Close-up view · located on the leg, arm and top or side of the foot · the subject is female: 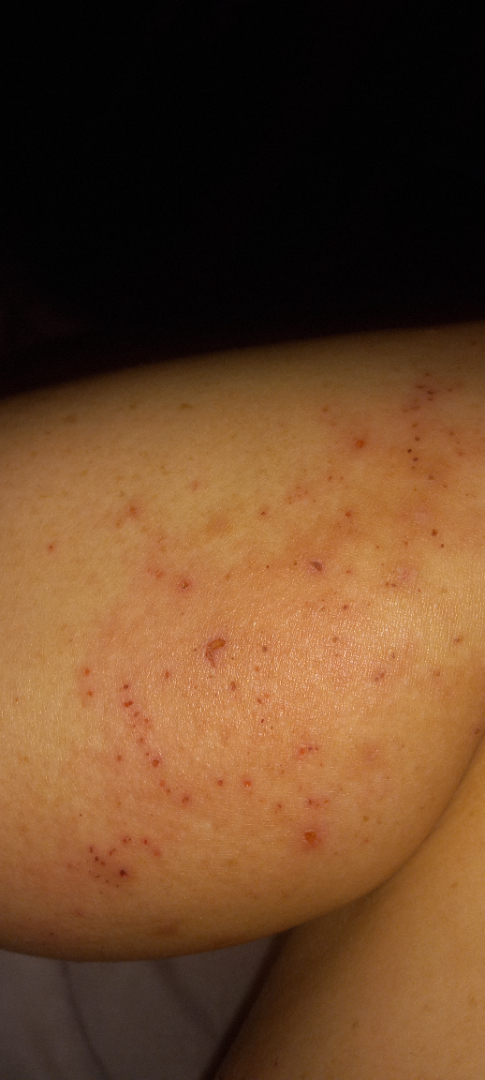  assessment: indeterminate from the photograph